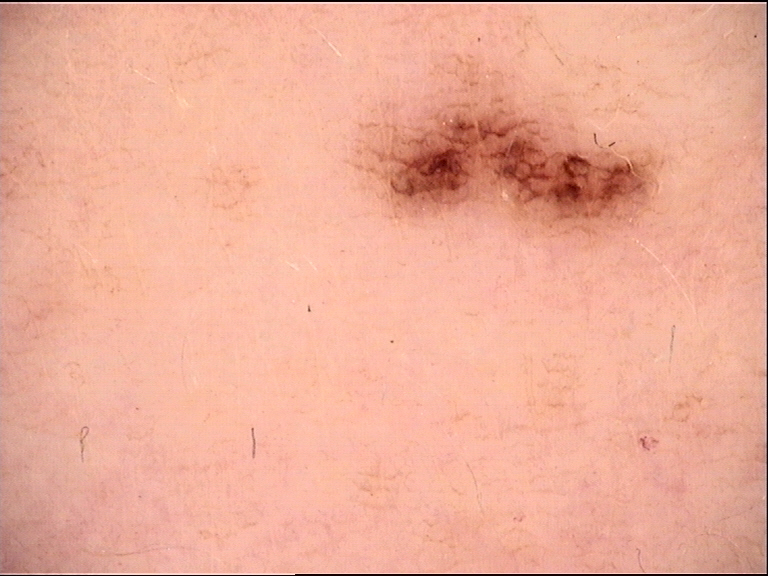{
  "image": "dermoscopy",
  "diagnosis": {
    "name": "dysplastic junctional nevus",
    "code": "jd",
    "malignancy": "benign",
    "super_class": "melanocytic",
    "confirmation": "expert consensus"
  }
}